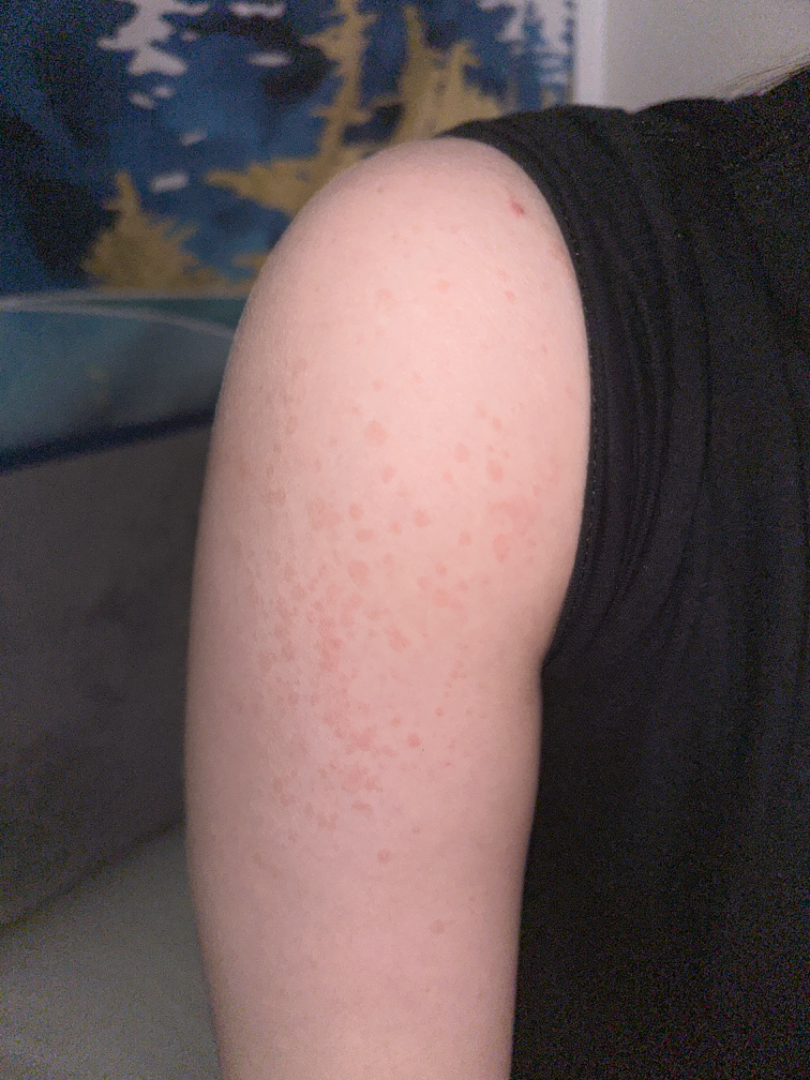Diagnostic features were not clearly distinguishable in this photograph. The lesion is described as rough or flaky. The photo was captured at a distance. Present for three to twelve months. The subject is 18–29, female. Self-categorized by the patient as a rash. Located on the arm.